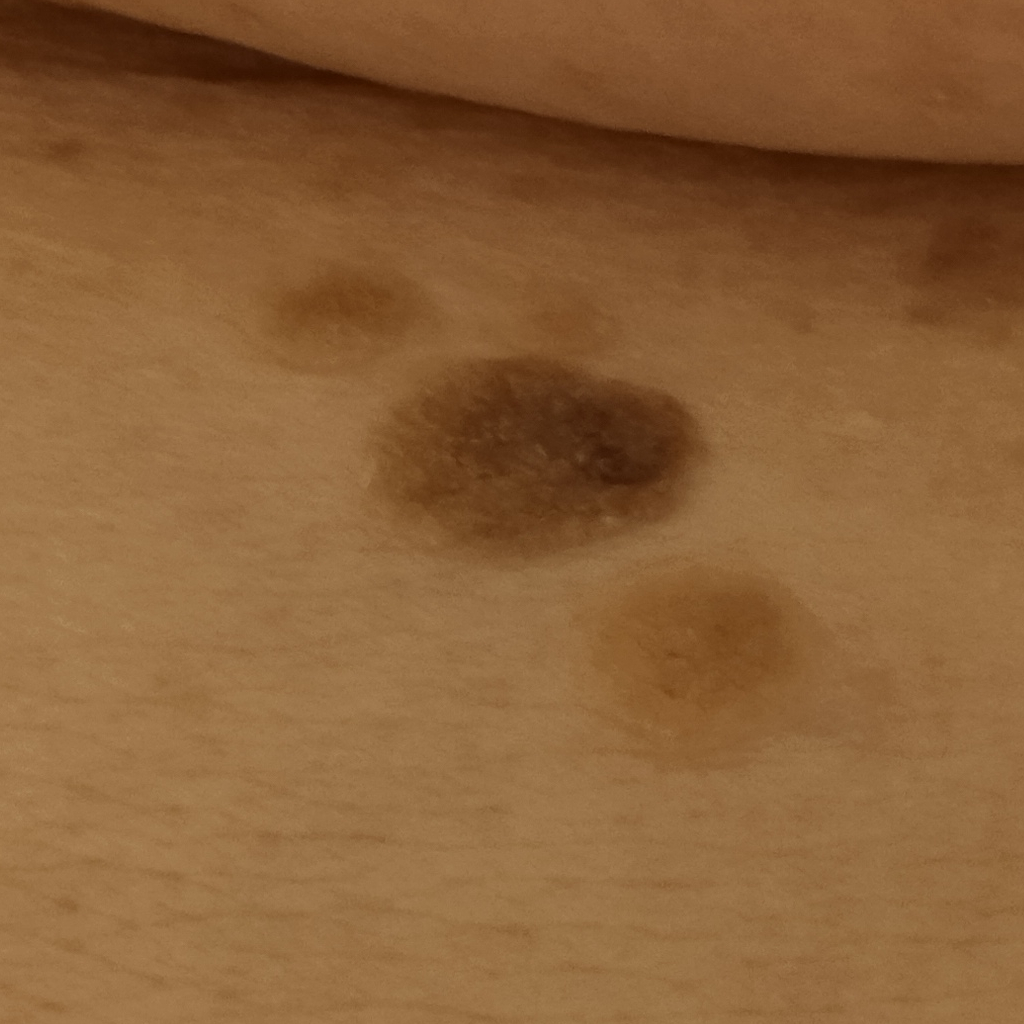sun reaction: skin reddens painfully with sun exposure
subject: female, aged 81
modality: clinical photograph
nevus count: a moderate number of melanocytic nevi
site: the torso
diameter: 12.2 mm
diagnosis: seborrheic keratosis (dermatologist consensus)